A moderate number of moles by the patient's own estimate. The patient reports no prior organ transplant and no sunbed use. The patient says their skin reddens with sun exposure. A female patient 20 years of age:
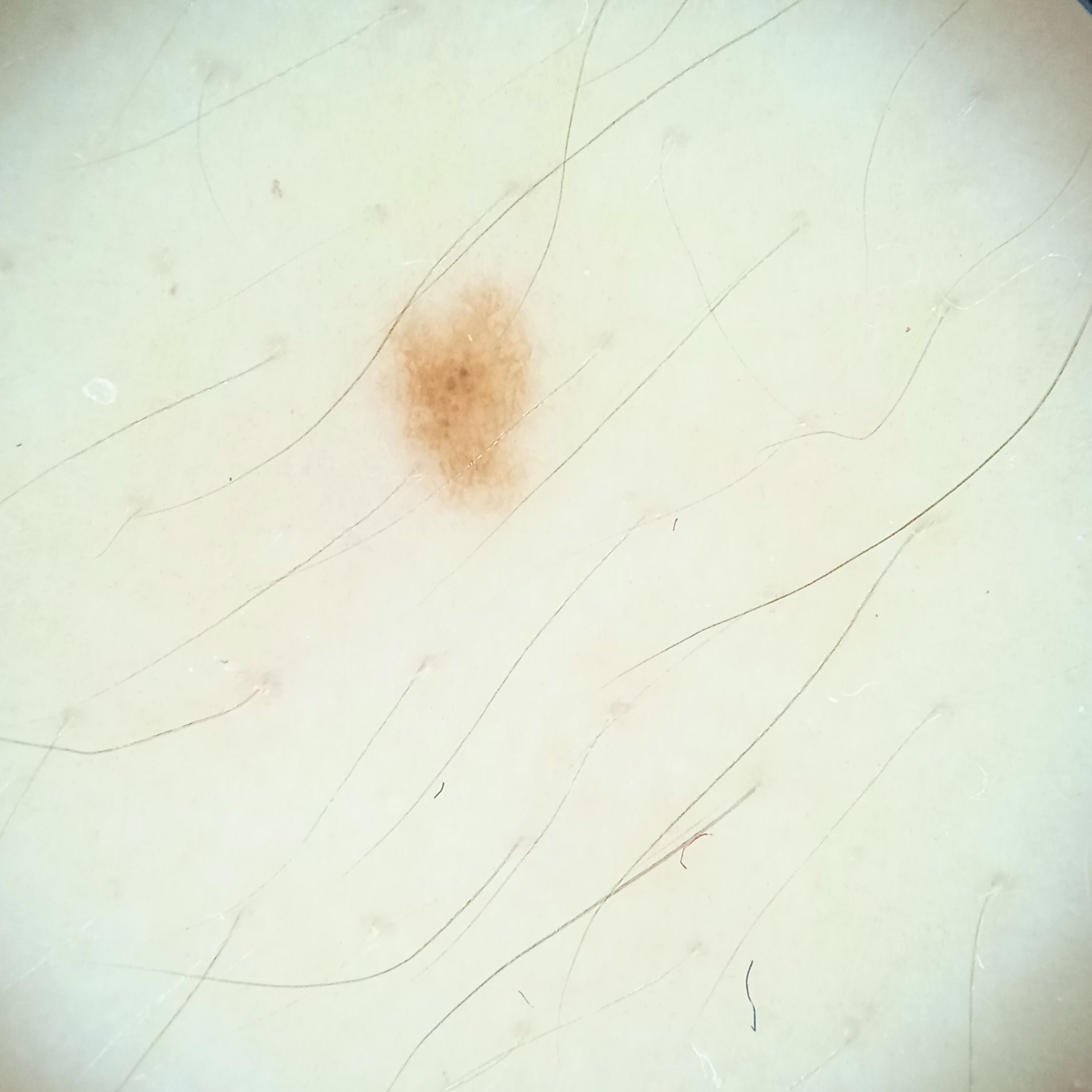<record>
  <diagnosis>
    <name>melanocytic nevus</name>
    <malignancy>benign</malignancy>
  </diagnosis>
</record>